An image taken at an angle · skin tone: FST IV; lay graders estimated 3 on the MST · symptoms reported: bothersome appearance, itching, enlargement and pain · the patient considered this a rash · reported duration is less than one week · the patient indicates associated fatigue — 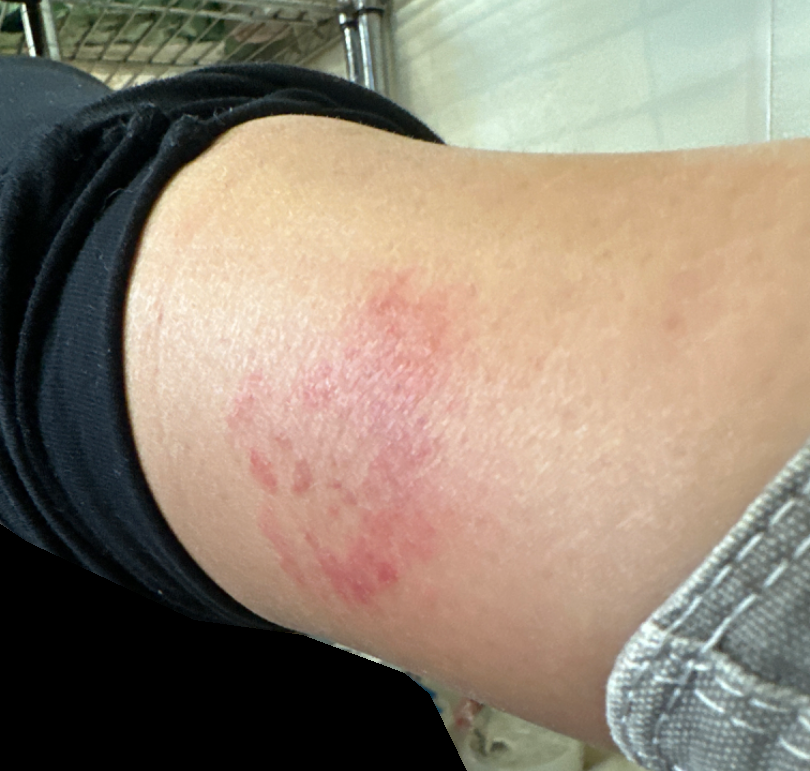The favored diagnosis is Irritant Contact Dermatitis; also raised was Acute dermatitis, NOS.